A dermoscopy image of a single skin lesion.
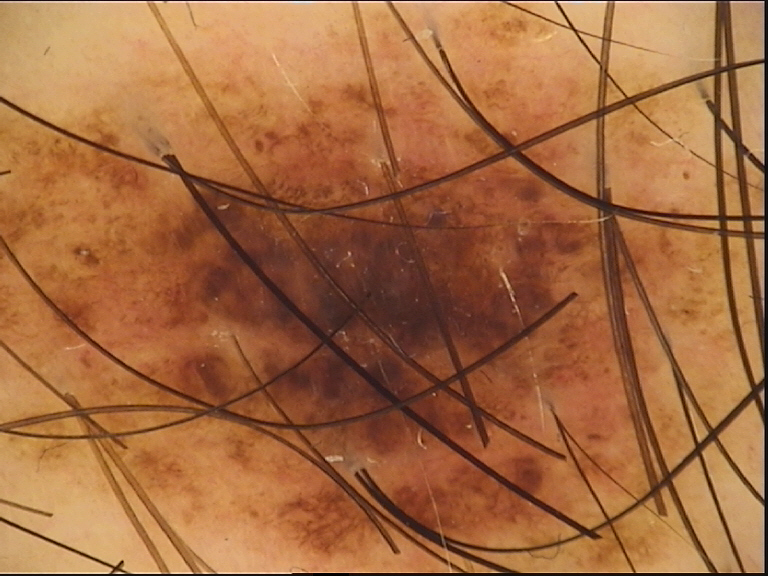Conclusion:
Classified as a benign lesion — a dysplastic compound nevus.